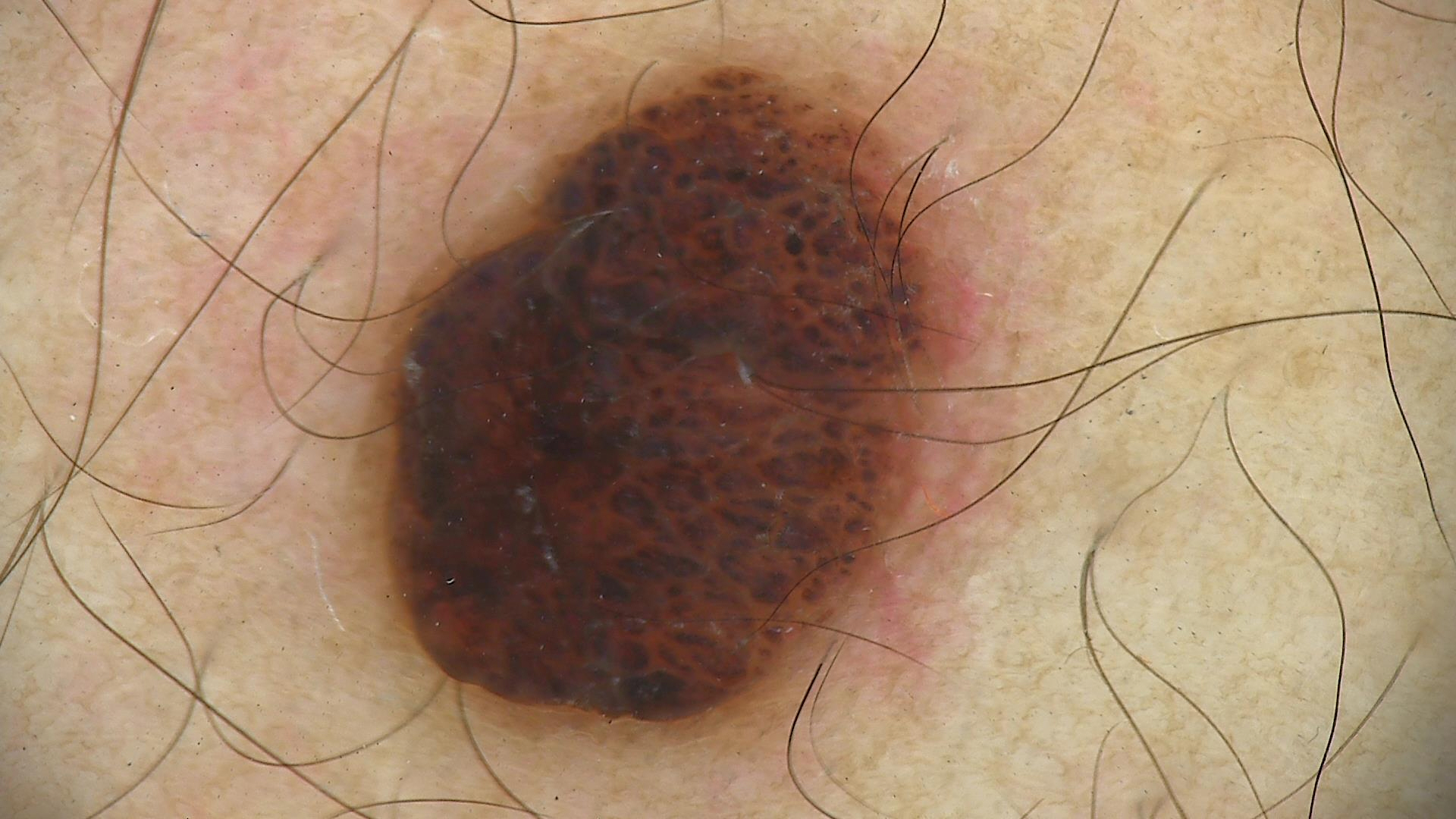A dermoscopic image of a skin lesion.
Classified as a compound nevus.